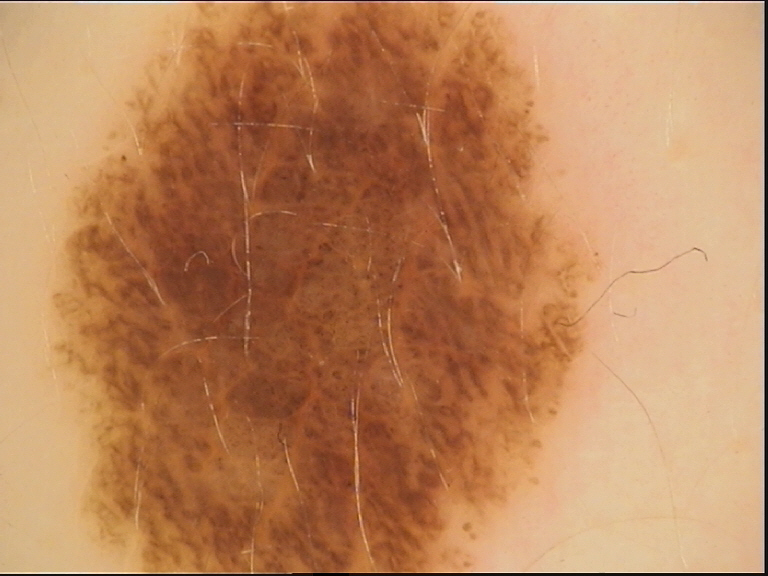Summary: A dermoscopy image of a single skin lesion. Impression: Classified as a benign lesion — a dysplastic compound nevus.